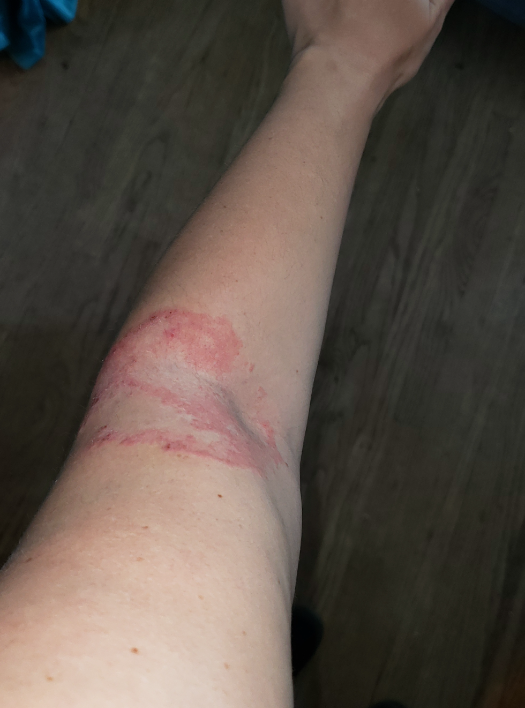The subject is a female aged 30–39. The affected area is the arm. The photo was captured at a distance. On teledermatology review, the leading impression is Tinea; less likely is Annular erythema; less probable is Eczema; a more distant consideration is Erythema annulare centrifugum; lower on the differential is Erythema gyratum repens.